This is a close-up image; the leg, front of the torso, head or neck, arm and back of the torso are involved; the contributor is a female aged 18–29.
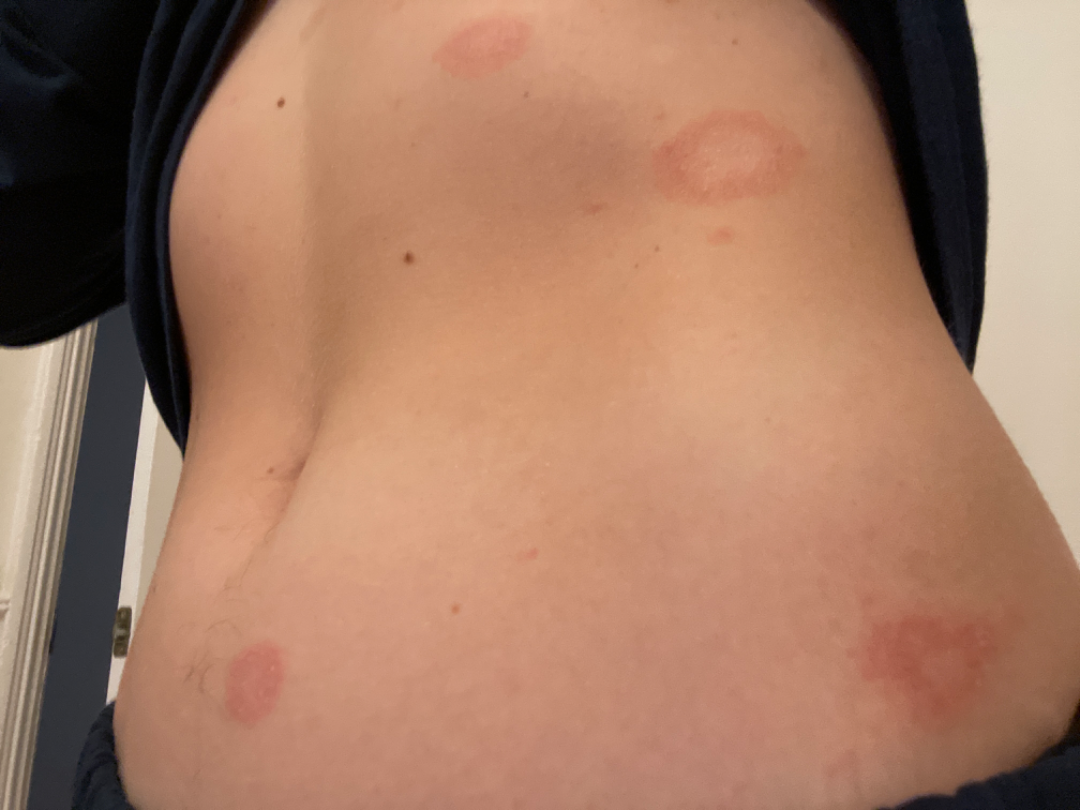Review:
The case was indeterminate on photographic review.